Skin tone: Fitzpatrick IV; non-clinician graders estimated Monk Skin Tone 3 (US pool) or 2 (India pool) · reported duration is less than one week · self-categorized by the patient as a rash · the lesion is described as fluid-filled · the arm and leg are involved · the photo was captured at a distance — 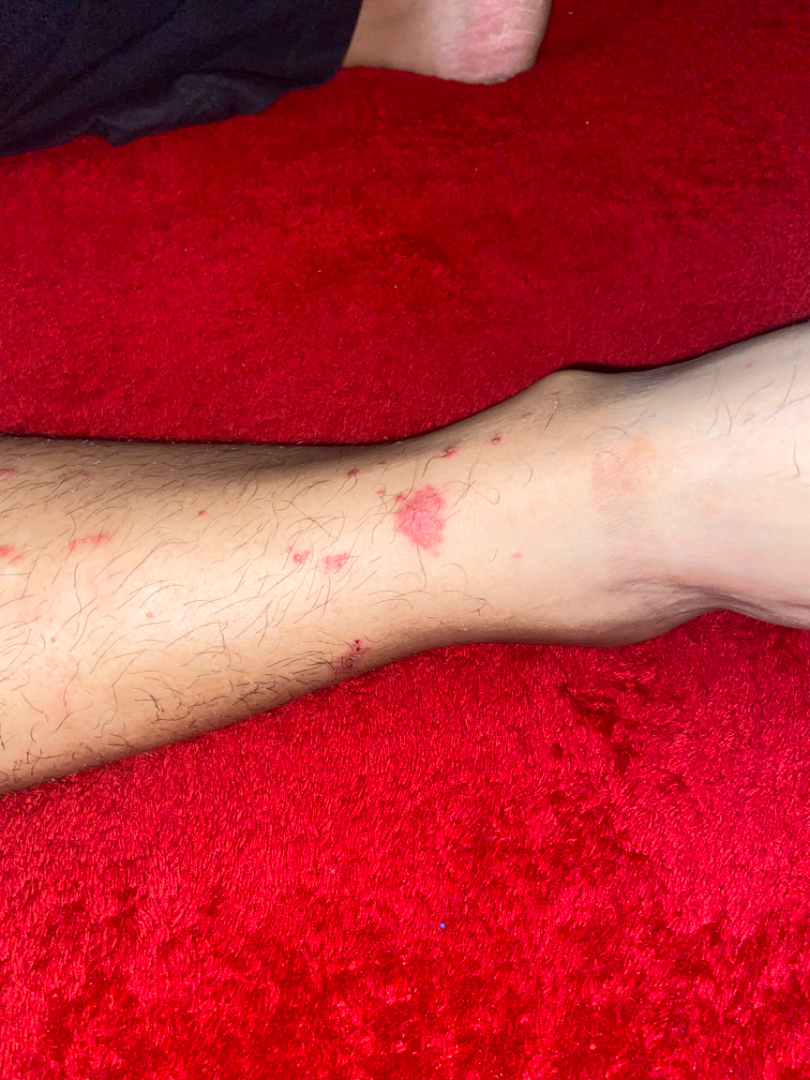<case>
<assessment>indeterminate from the photograph</assessment>
</case>